The patient described the issue as skin that appeared healthy to them. The back of the torso is involved. The patient reported no relevant symptoms from the lesion. Present for one to three months. Close-up view. The patient indicates the lesion is flat:
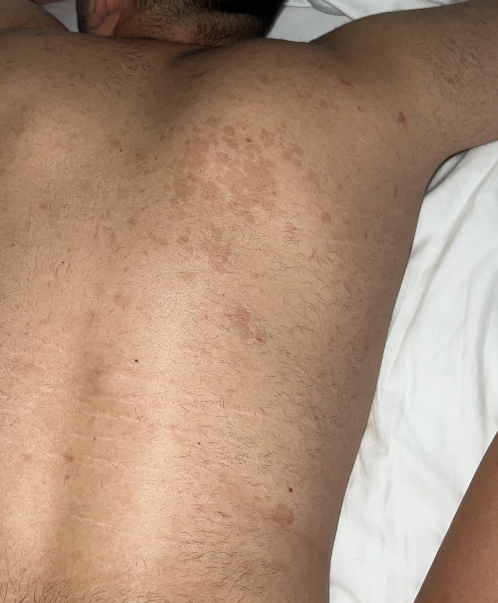differential diagnosis = a single dermatologist reviewed the case: most likely Tinea Versicolor; possibly Pityriasis alba; with consideration of Confluent and reticulate papillomatosis.